A close-up photograph · the head or neck is involved · the contributor is 70–79, female:
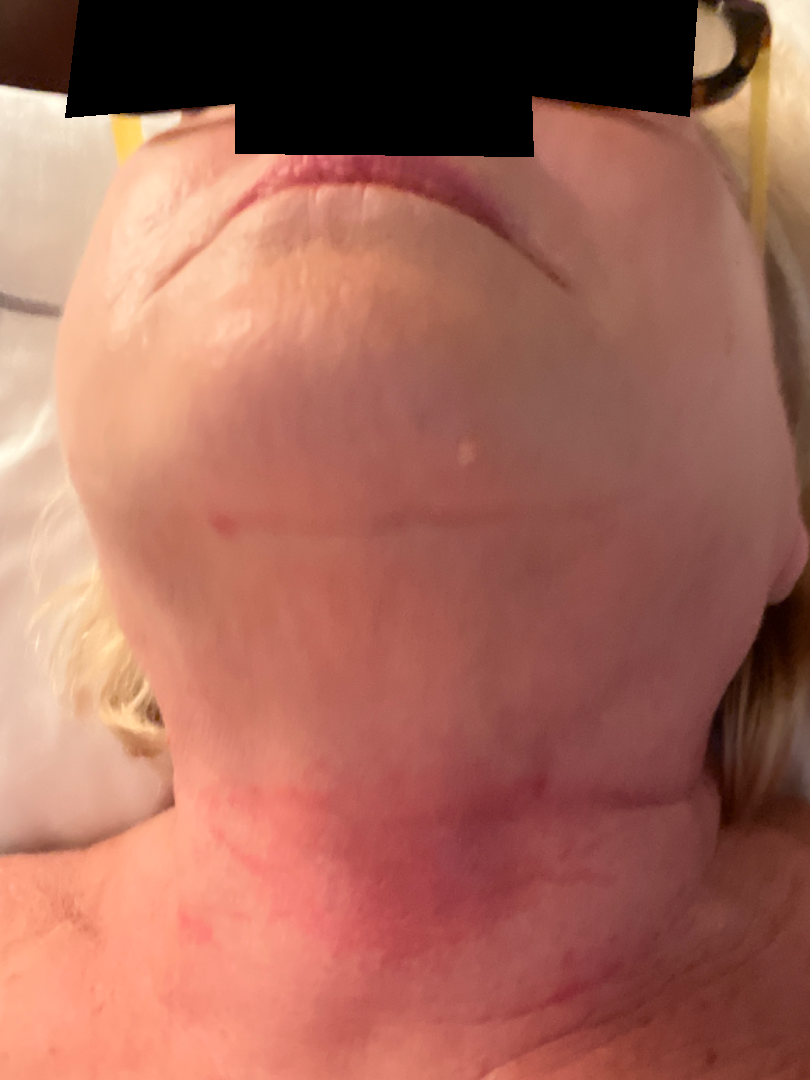Assessment: The skin condition could not be confidently assessed from this image. Clinical context: The patient notes the lesion is flat. Lay reviewers estimated a Monk skin tone scale of 2. Reported duration is less than one week. Reported lesion symptoms include burning.